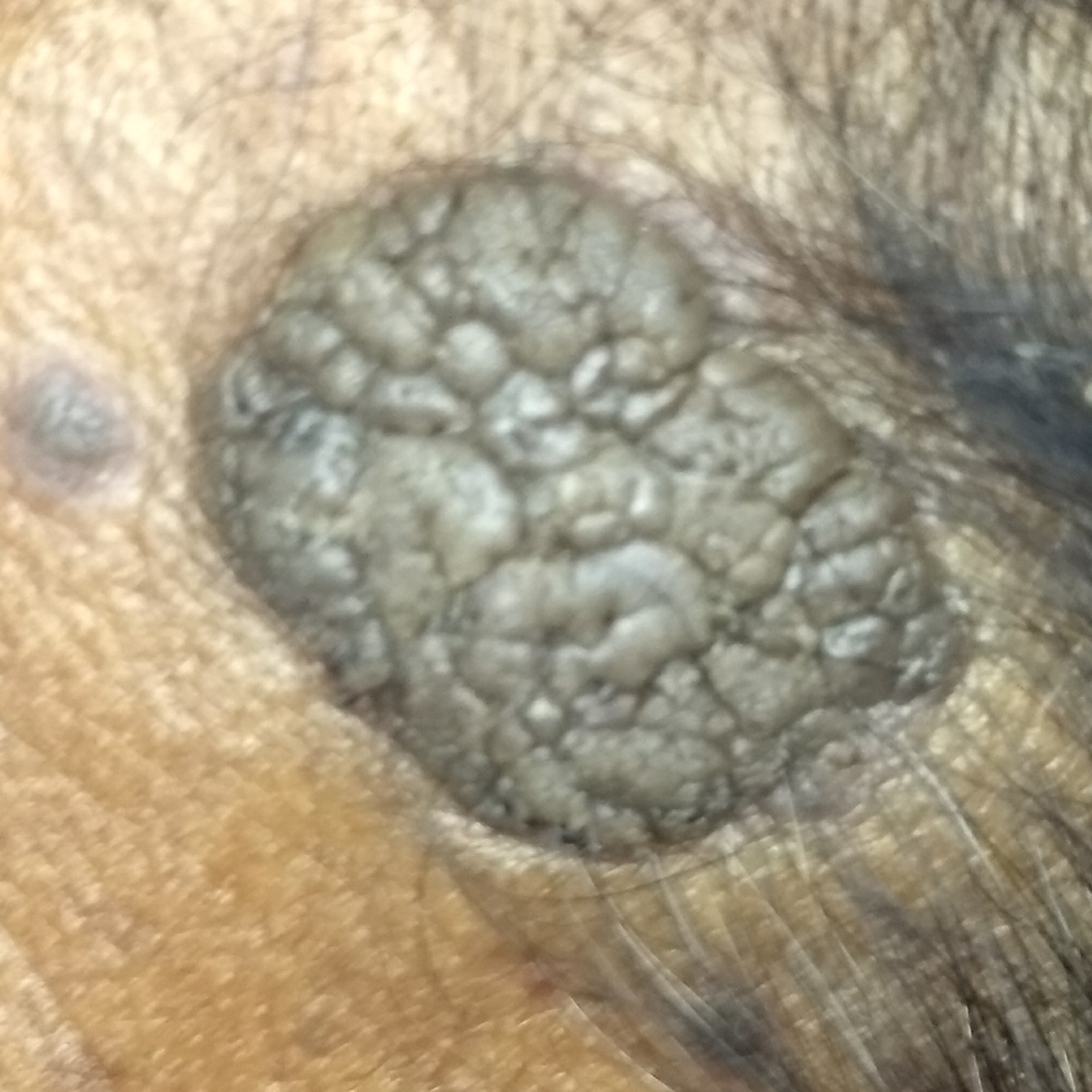| feature | finding |
|---|---|
| modality | clinical photo |
| patient | 73 years of age |
| location | the face |
| assessment | seborrheic keratosis (clinical consensus) |